A close-up photograph:
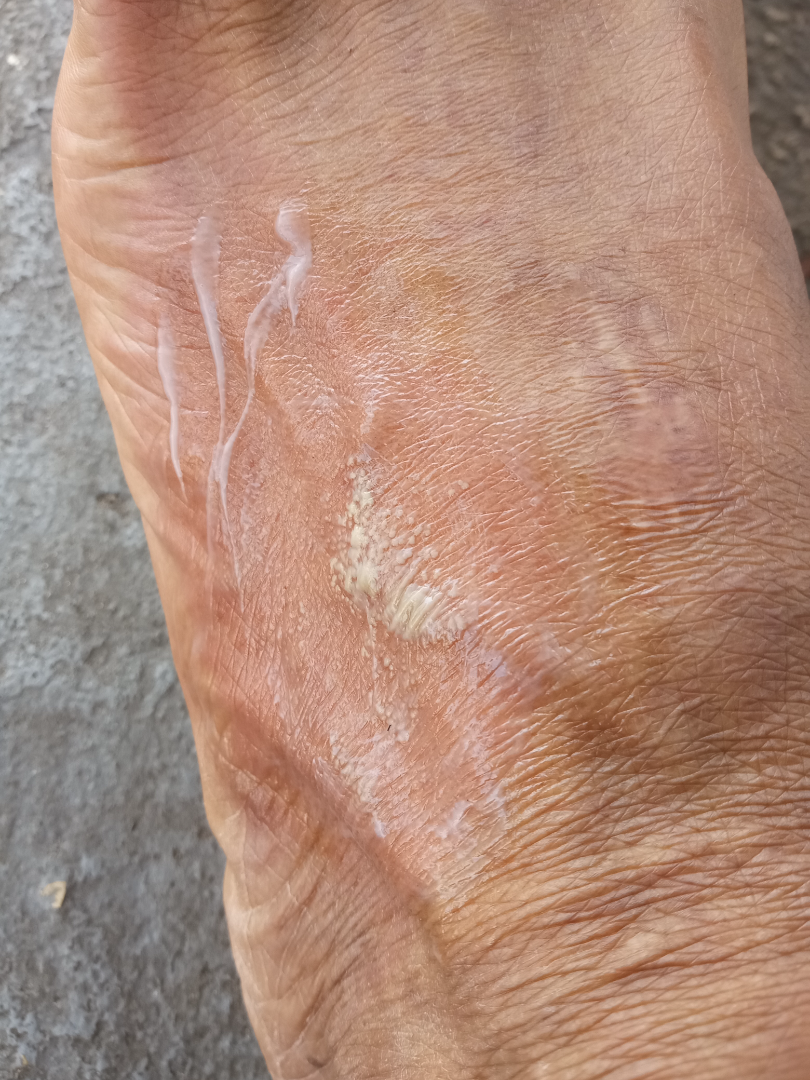assessment: unable to determine.